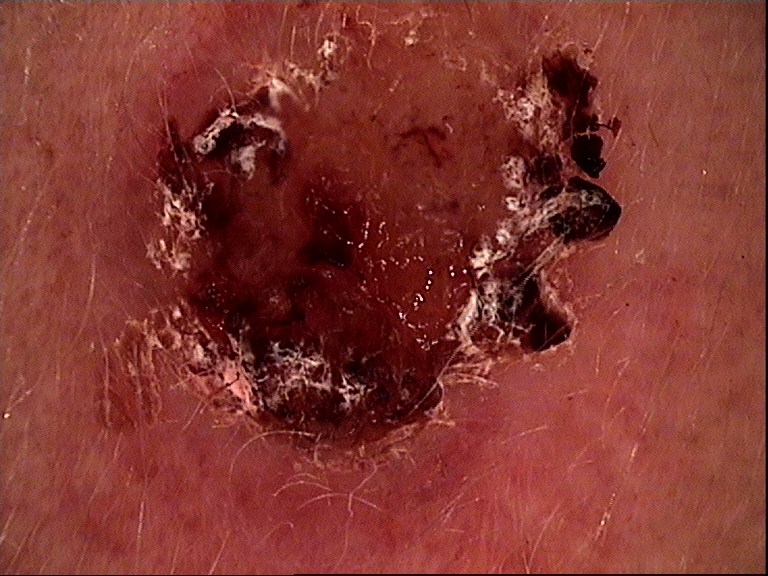Summary: A skin lesion imaged with a dermatoscope. The architecture is that of a keratinocytic lesion. Conclusion: Confirmed on histopathology as a squamous cell carcinoma.